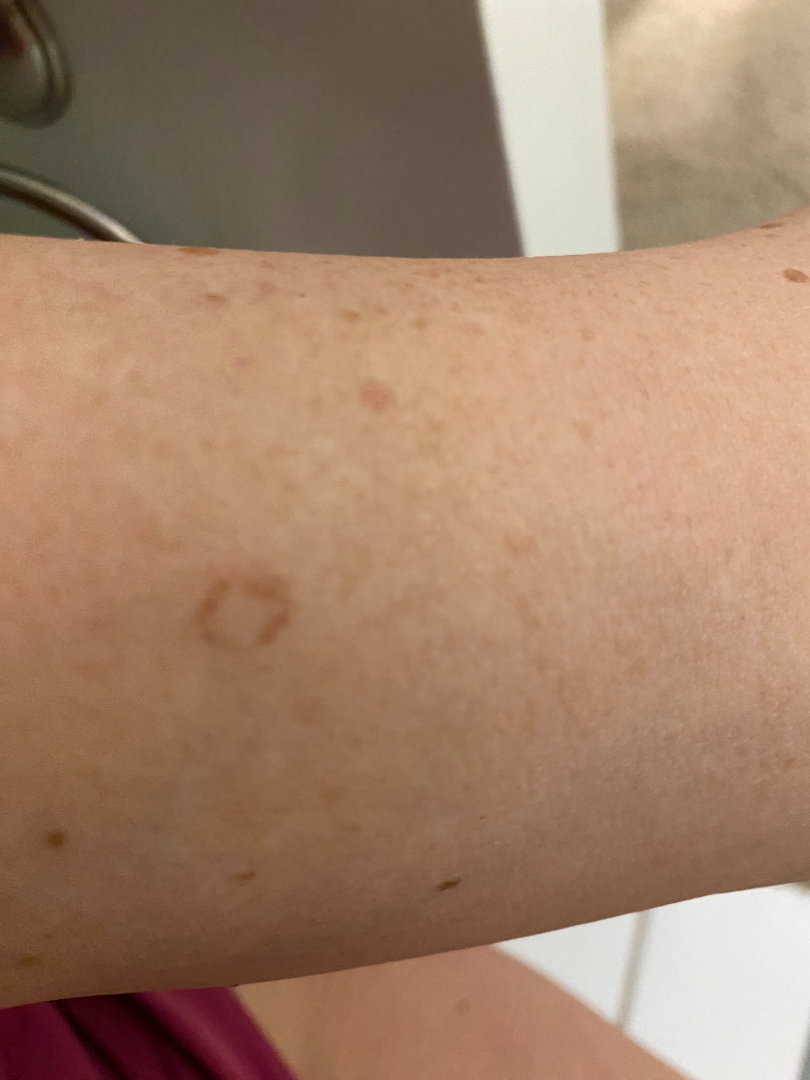contributor: female, age 50–59 | history: less than one week | anatomic site: arm | self-categorized as: a rash | reported symptoms: none reported | associated systemic symptoms: none reported | framing: close-up | surface texture: flat.